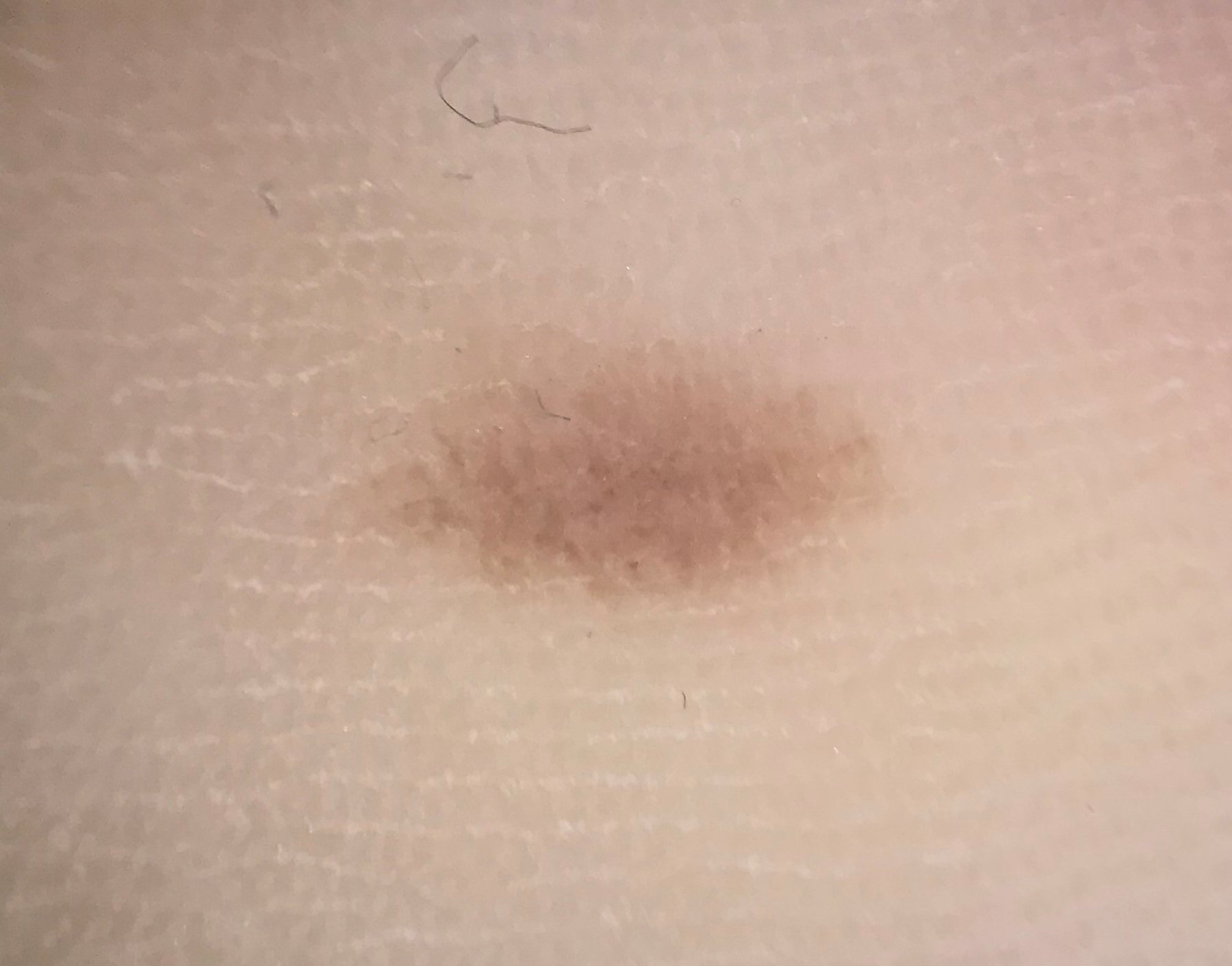Findings: This is a banal lesion. Impression: Classified as an acral junctional nevus.